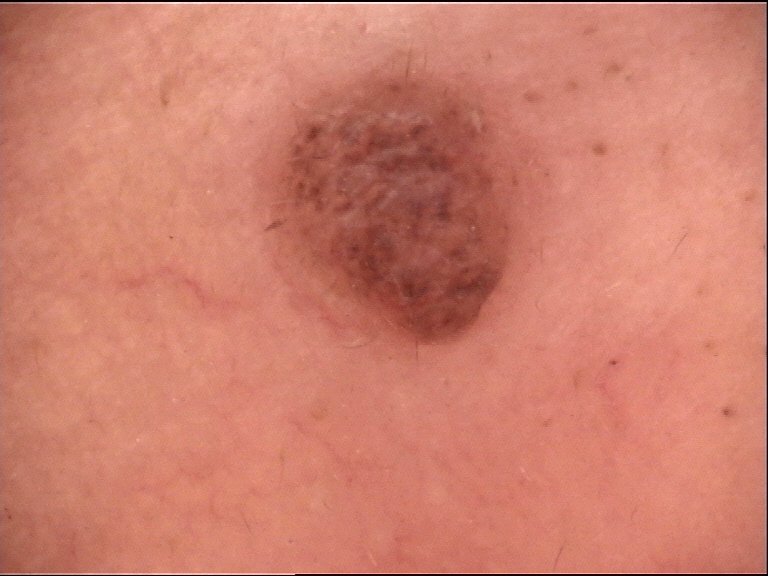Summary:
A dermoscopic photograph of a skin lesion. The morphology is that of a banal lesion.
Conclusion:
Diagnosed as a dermal nevus.